A smartphone photograph of a skin lesion; a subject 55 years of age: 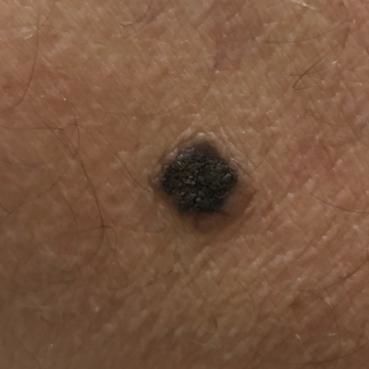The lesion involves the back. Per patient report, the lesion has grown and is elevated. The consensus clinical diagnosis was a nevus.